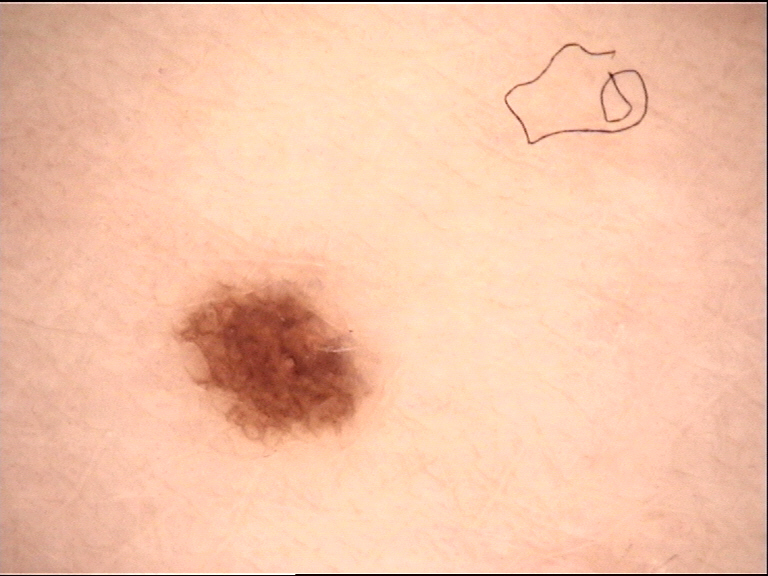A dermatoscopic image of a skin lesion.
Labeled as a dysplastic junctional nevus.